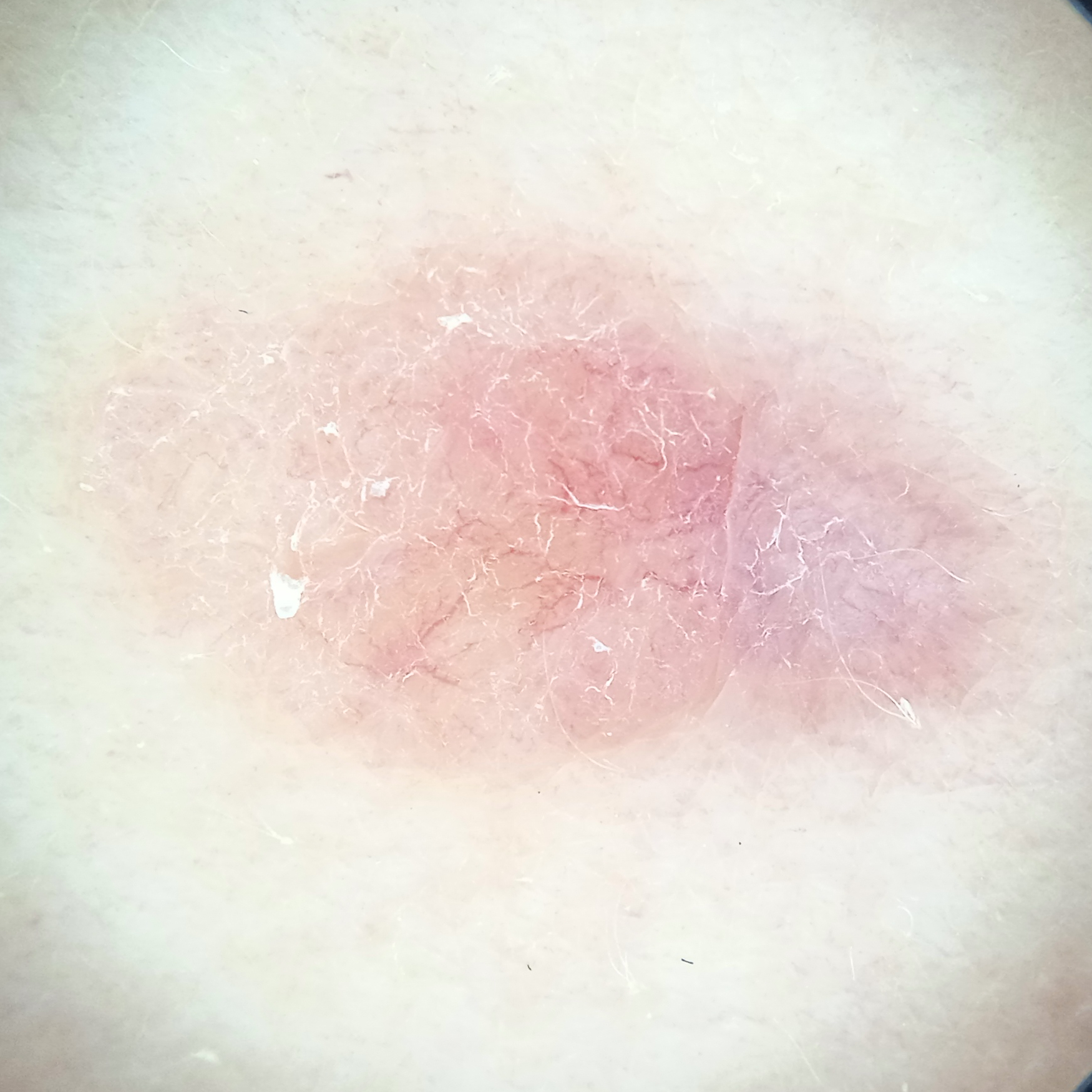Few moles overall by the patient's own estimate. The patient reports a history of sunbed use, a family history of skin cancer, no prior organ transplant, and no immunosuppression. A skin lesion imaged with a dermatoscope. A female subject age 48. The patient says their skin reddens painfully with sun exposure. Measuring roughly 12.3 mm. Histopathology confirmed a basal cell carcinoma, following excision, with a measured thickness of 1.1 mm.